This image was taken at an angle, the affected area is the leg, the subject is female:
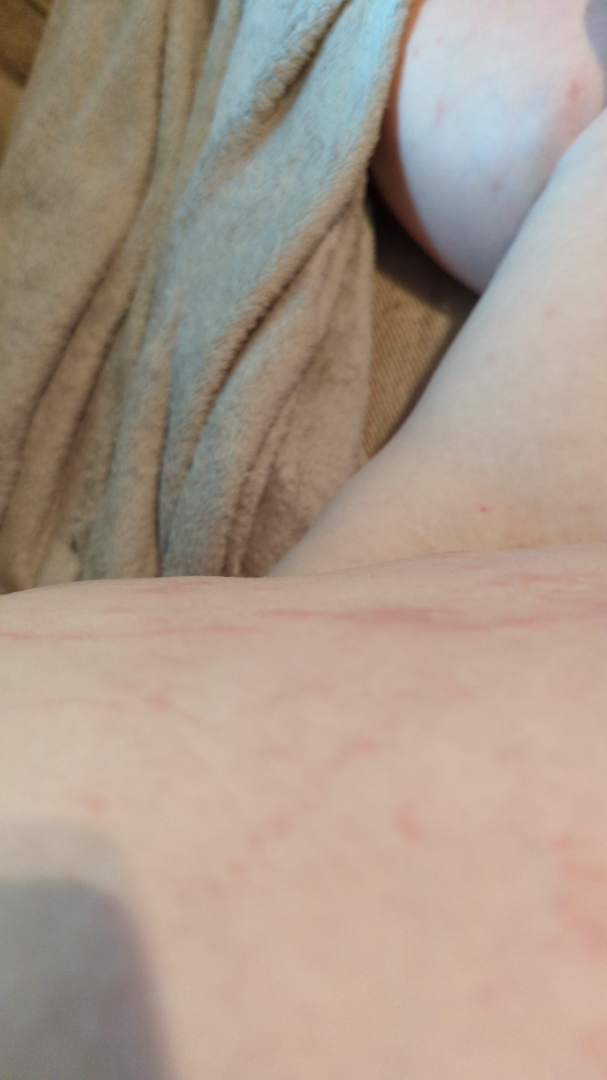Case summary:
• clinical impression — most consistent with Hypersensitivity; also consider Eczema; an alternative is Allergic Contact Dermatitis; less likely is Inflicted skin lesions; less probable is Urticaria; lower on the differential is Flagellate erythema